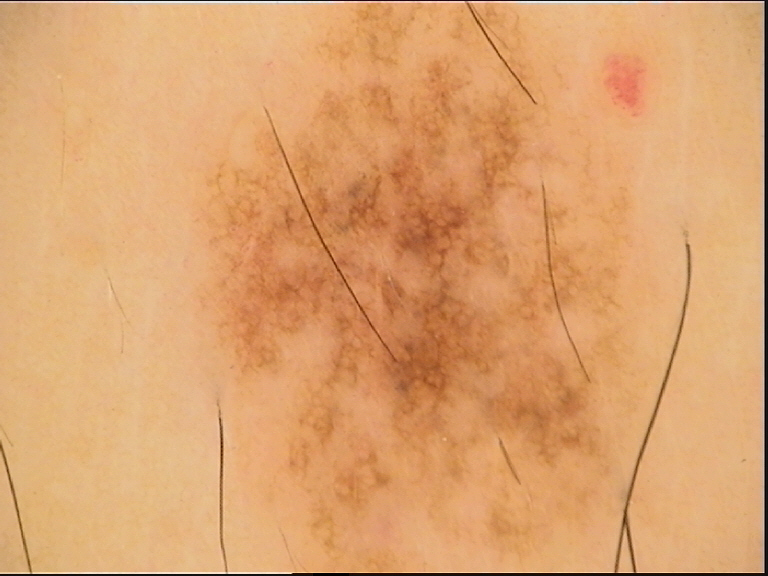Conclusion:
Labeled as a dysplastic junctional nevus.